The subject is female. The affected area is the arm. Close-up view.
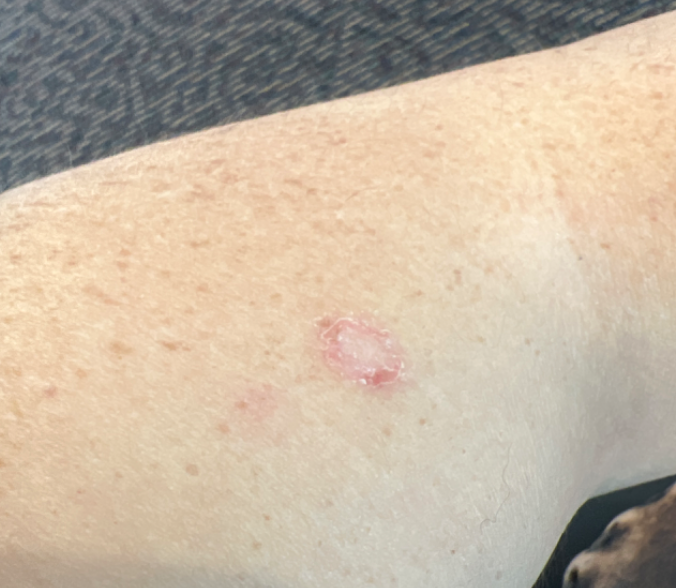assessment — indeterminate from the photograph | present for — one to four weeks | skin tone — Fitzpatrick phototype II; lay reviewers estimated Monk skin tone scale 2 or 3 | systemic symptoms — none reported | lesion symptoms — bothersome appearance and enlargement | described texture — rough or flaky.